The patient reports bothersome appearance. Close-up view. Texture is reported as fluid-filled and raised or bumpy. The affected area is the front of the torso. The patient reports the condition has been present for less than one week. The subject is 18–29, male. The patient described the issue as a rash.
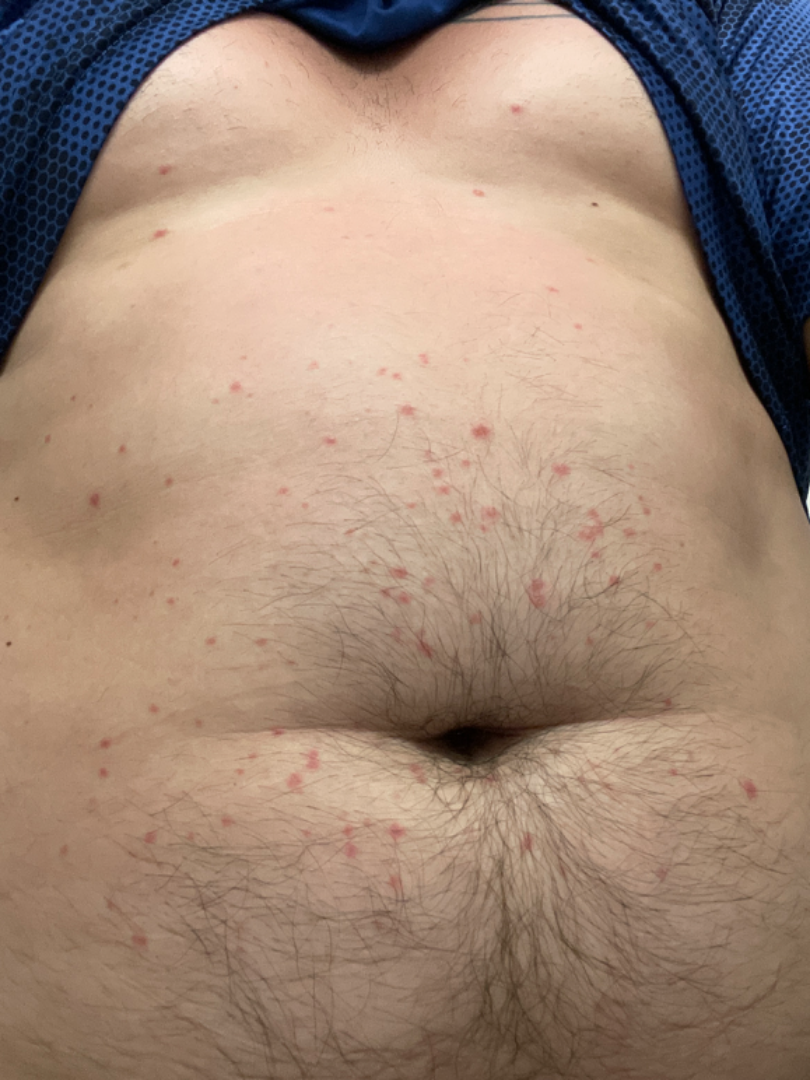assessment: unable to determine